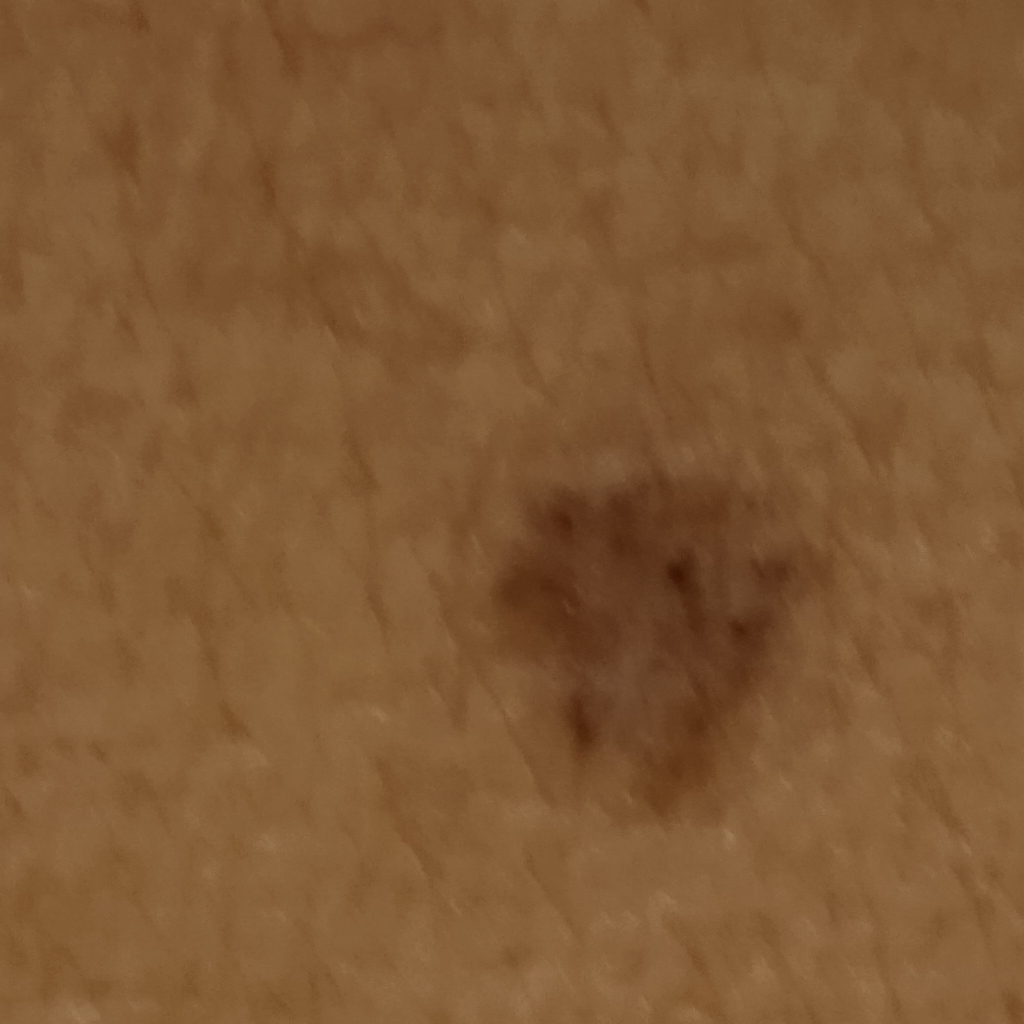Findings:
* image type: clinical photograph
* sun reaction: skin tans without first burning
* nevus count: few melanocytic nevi overall
* referral: clinical suspicion of basal cell carcinoma
* subject: female, aged 60
* relevant history: a personal history of skin cancer, a personal history of cancer
* body site: the torso
* diameter: 7.2 mm
* assessment: basal cell carcinoma (dermatologist consensus)